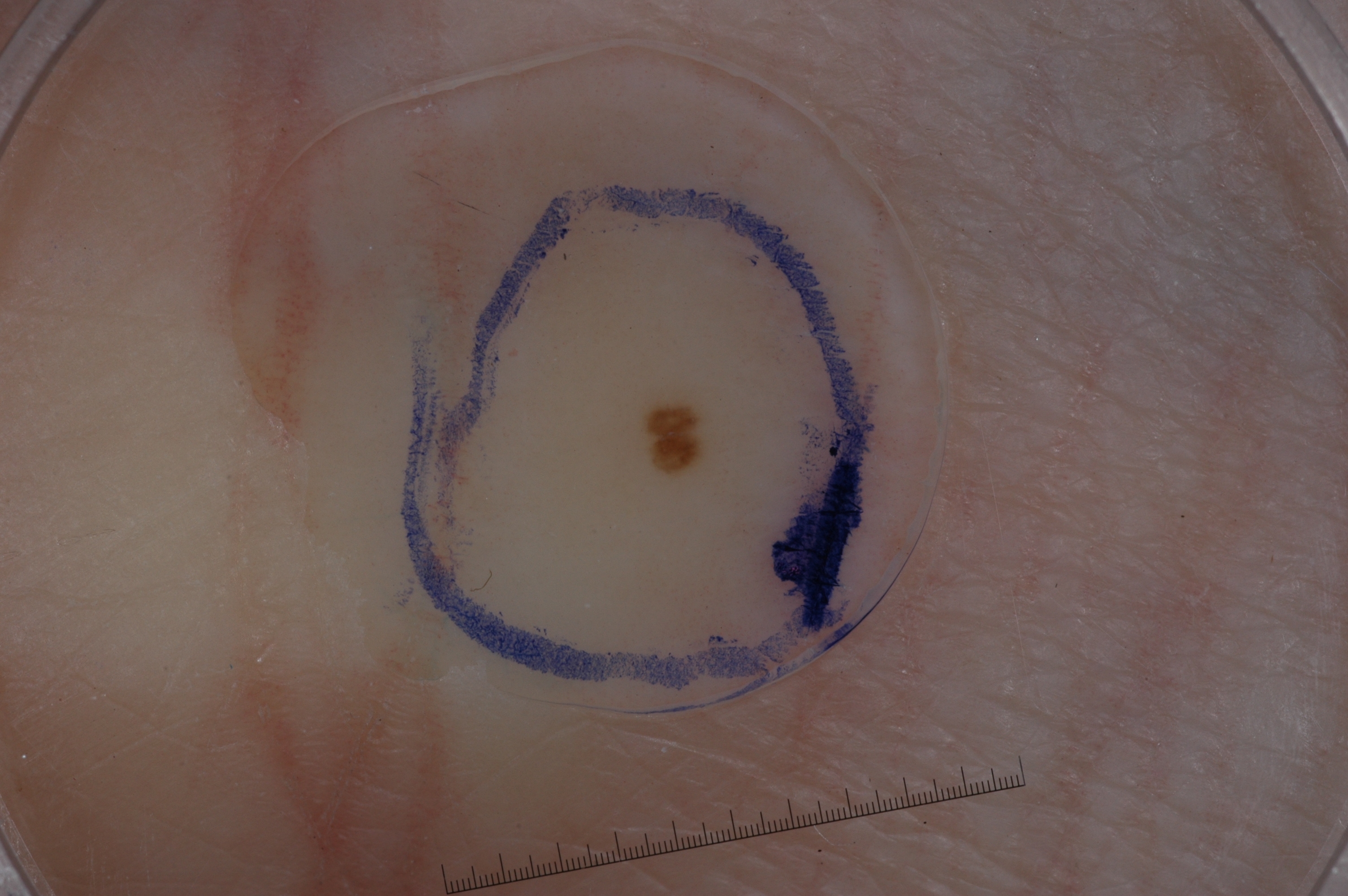A female subject in their mid- to late 40s.
A dermoscopic image of a skin lesion.
A small lesion occupying a minor part of the field.
As (left, top, right, bottom), the lesion is bounded by (637, 391, 709, 479).
Dermoscopically, the lesion shows no milia-like cysts, negative network, pigment network, or streaks.
The lesion was assessed as a melanocytic nevus.